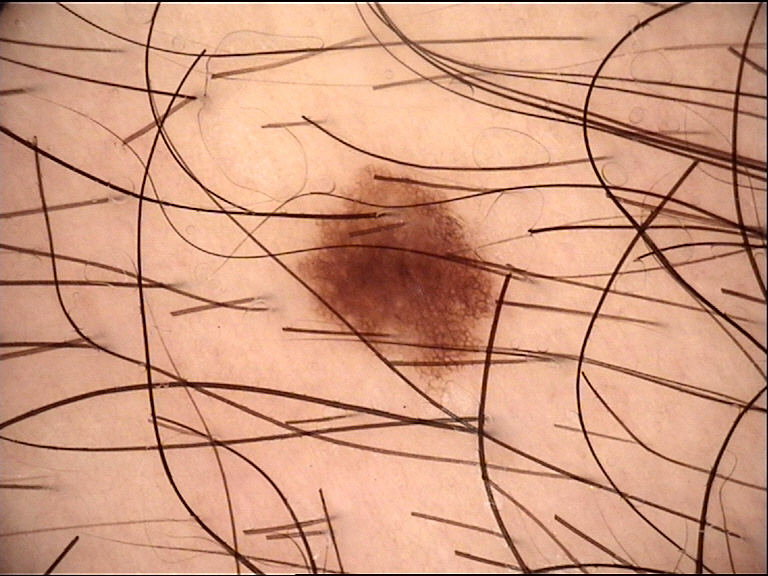diagnosis = dysplastic junctional nevus (expert consensus).